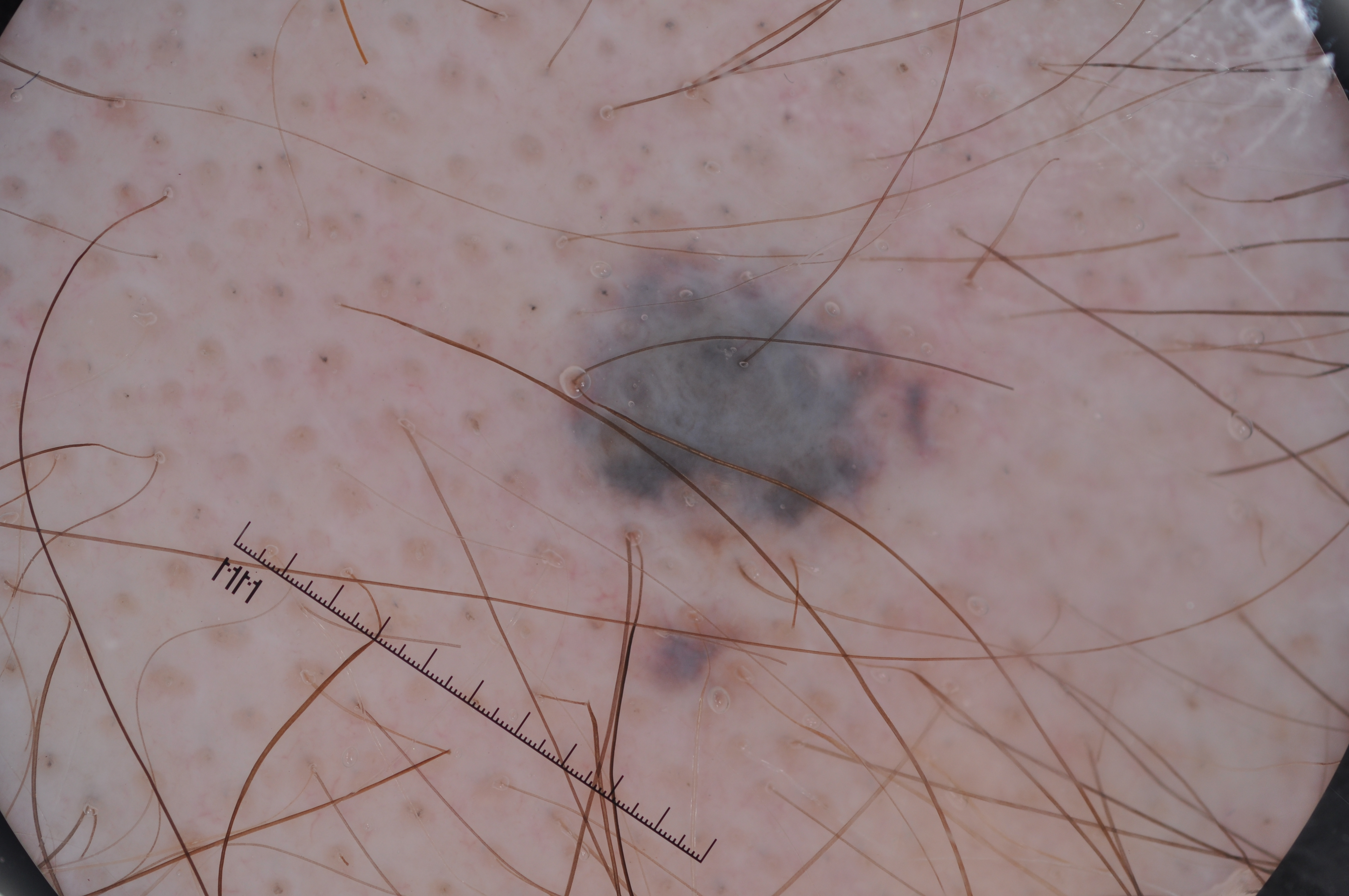image:
  modality: dermoscopy
lesion_location:
  bbox_xyxy:
    - 541
    - 201
    - 965
    - 713
diagnosis:
  name: melanocytic nevus
  malignancy: benign
  lineage: melanocytic
  provenance: clinical